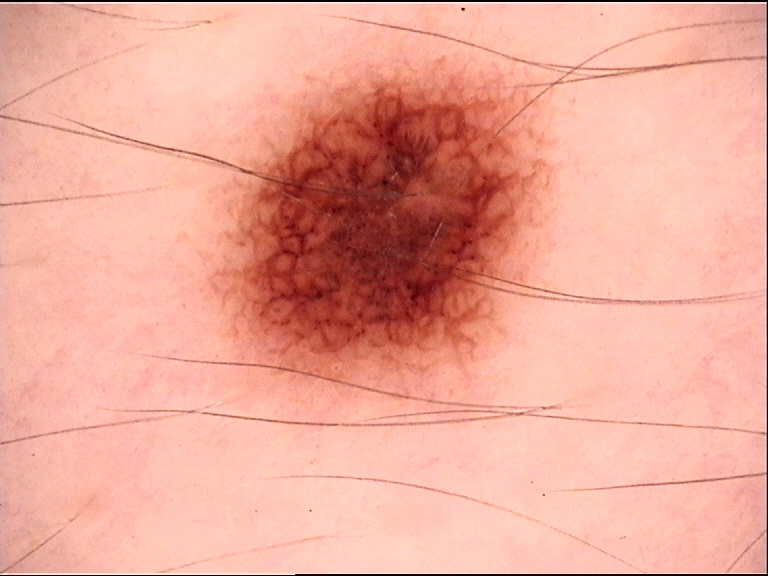Dermoscopy of a skin lesion.
Classified as a dysplastic junctional nevus.